A male patient aged around 80; dermoscopy of a skin lesion; the patient was assessed as skin type II.
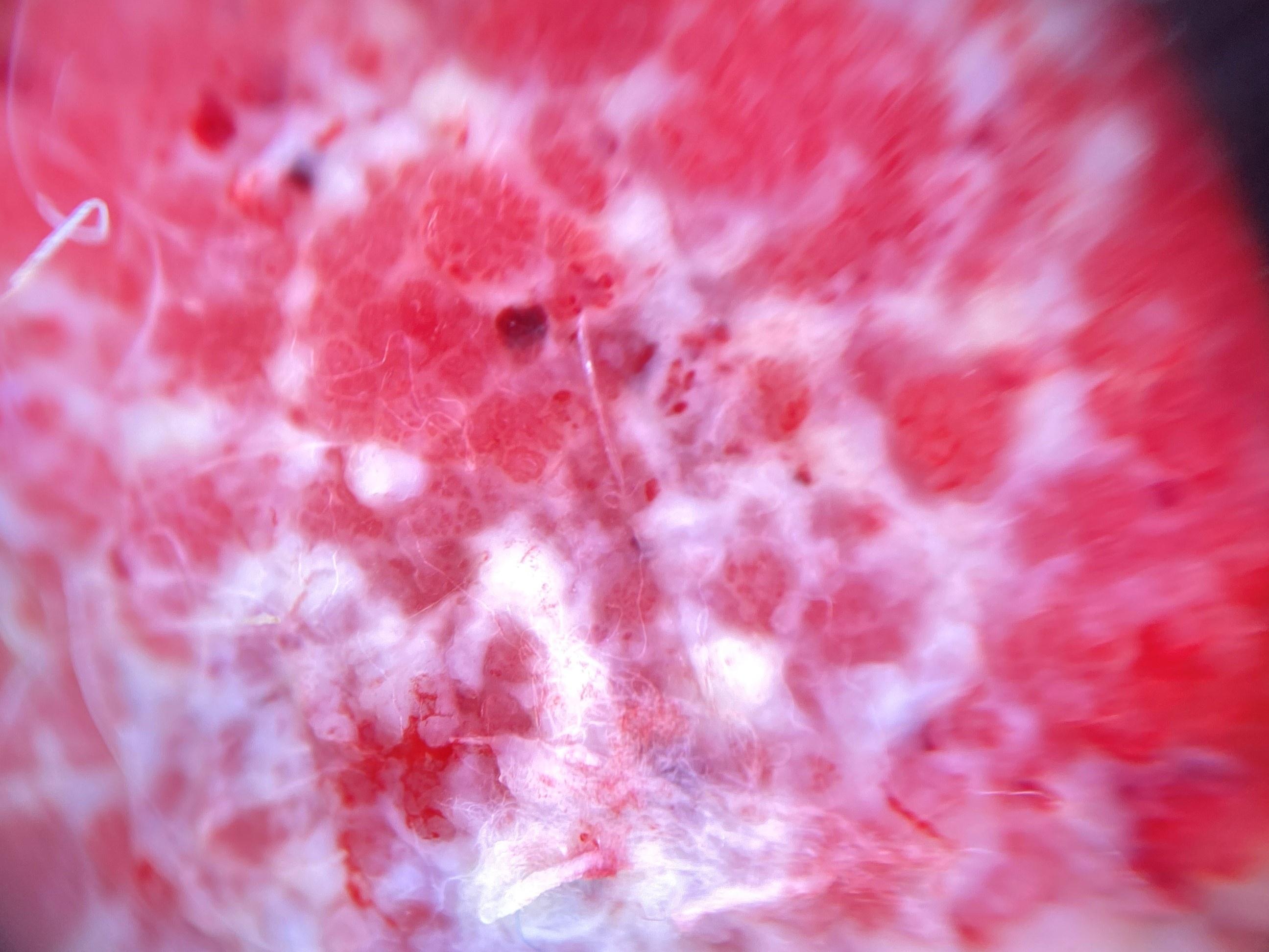Biopsy-confirmed as a skin cancer — a squamous cell carcinoma.